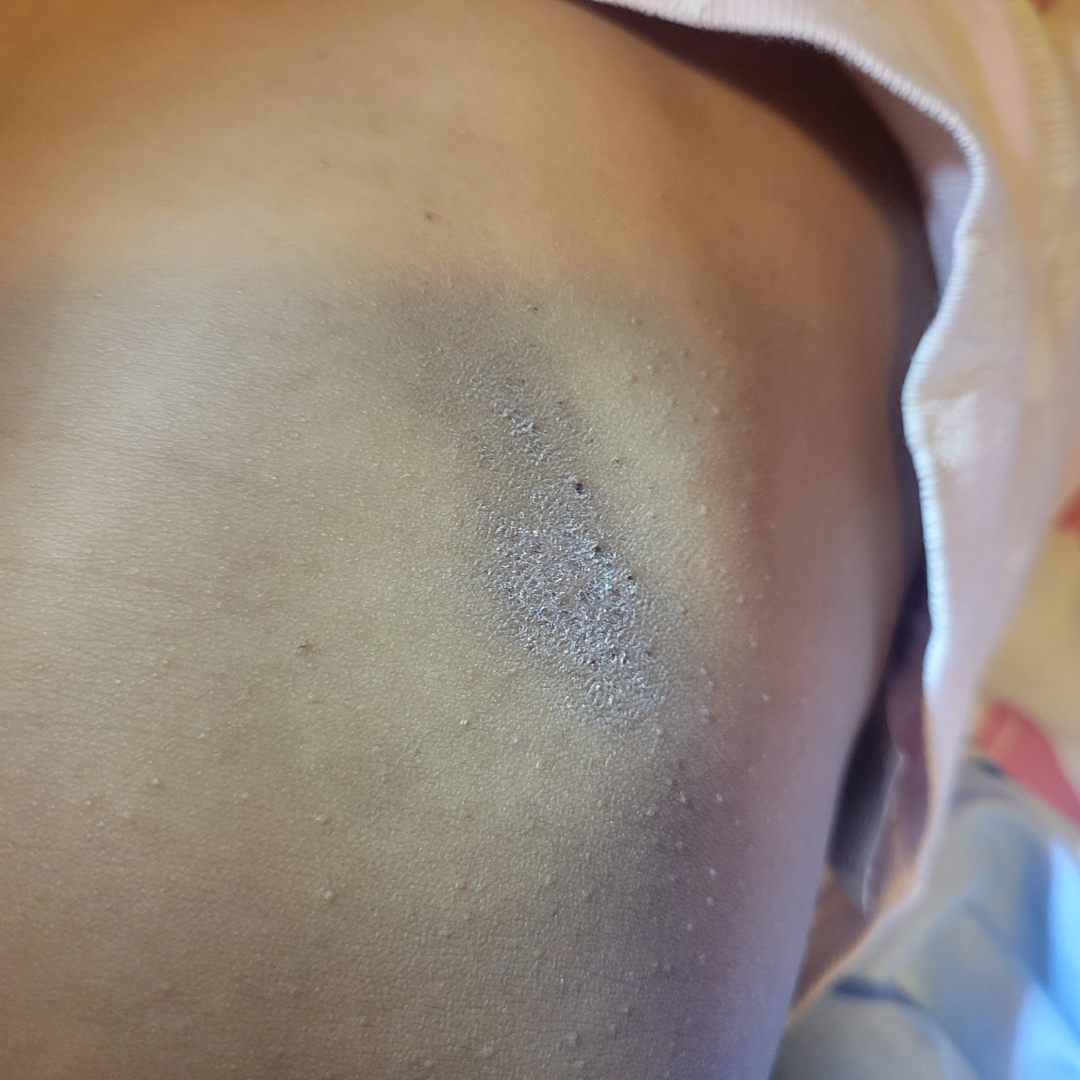The photograph is a close-up of the affected area. On remote review of the image, most consistent with Chronic dermatitis, NOS.